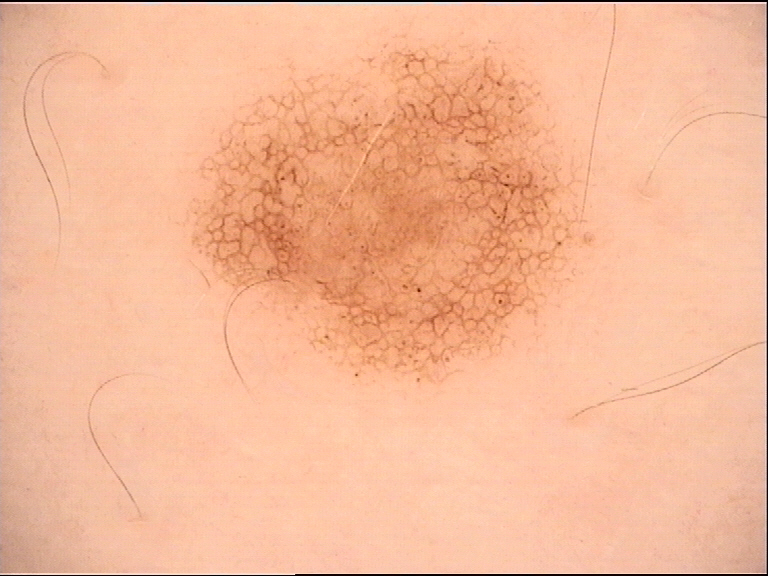The diagnosis was a dysplastic junctional nevus.